This is a close-up image — 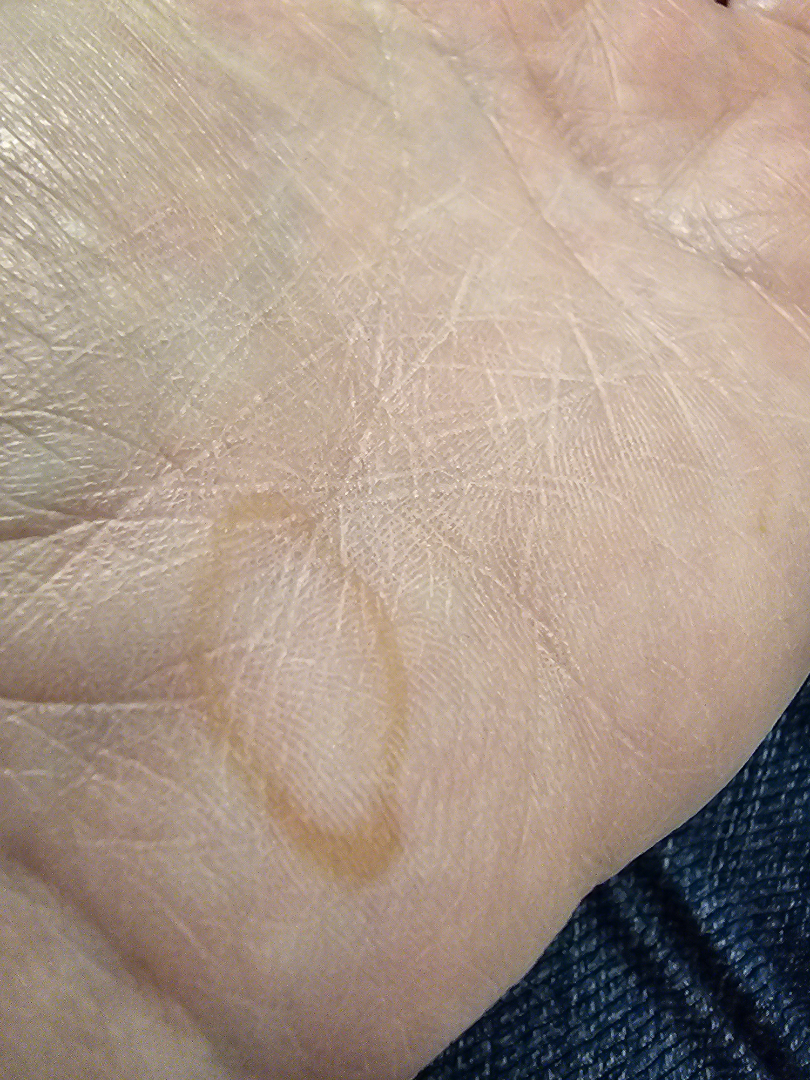One reviewing dermatologist: the reviewer's impression was Traumatic blister.